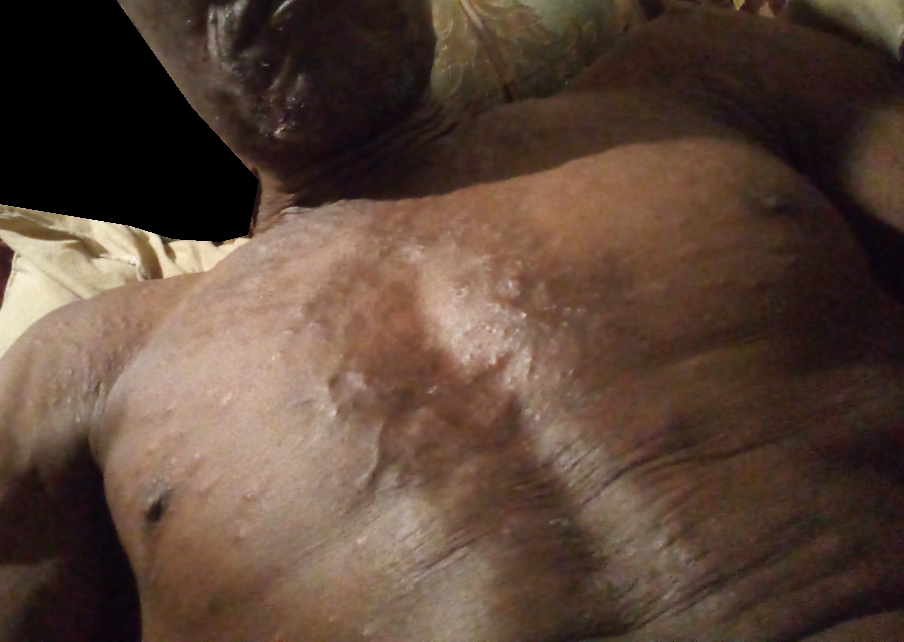Notes:
* assessment · indeterminate from the photograph
* self-categorized as · a rash
* image framing · at an angle
* history · one to four weeks
* patient-reported symptoms · itching and enlargement
* described texture · raised or bumpy, fluid-filled and rough or flaky
* location · arm, head or neck and front of the torso